A male patient in their 60s. The chart records prior malignancy (patient or family), alcohol use, and tobacco use.
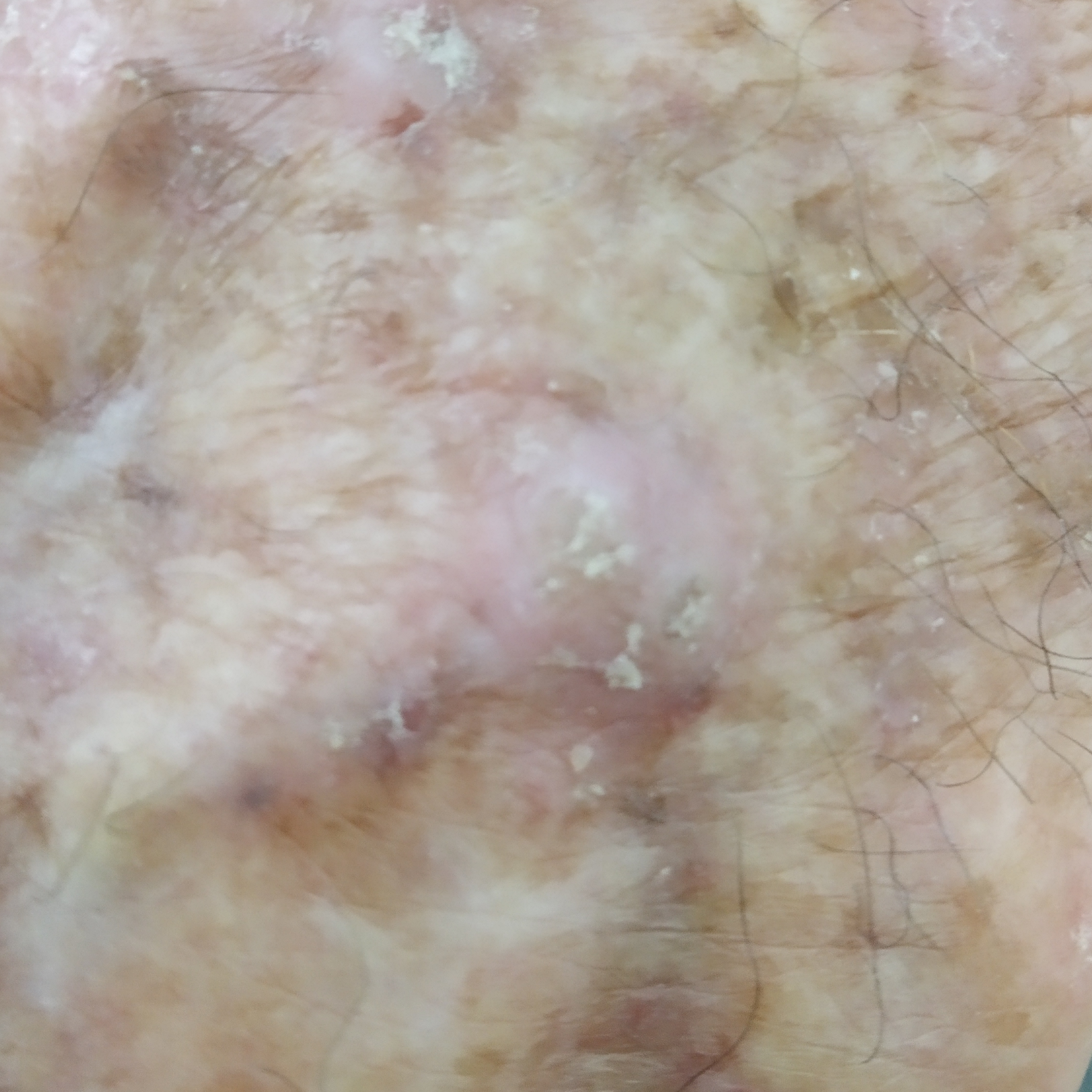The lesion involves a hand.
The lesion measures 10 × 9 mm.
Per patient report, the lesion itches, has changed, has grown, and is elevated, but does not hurt.
Histopathology confirmed a squamous cell carcinoma.